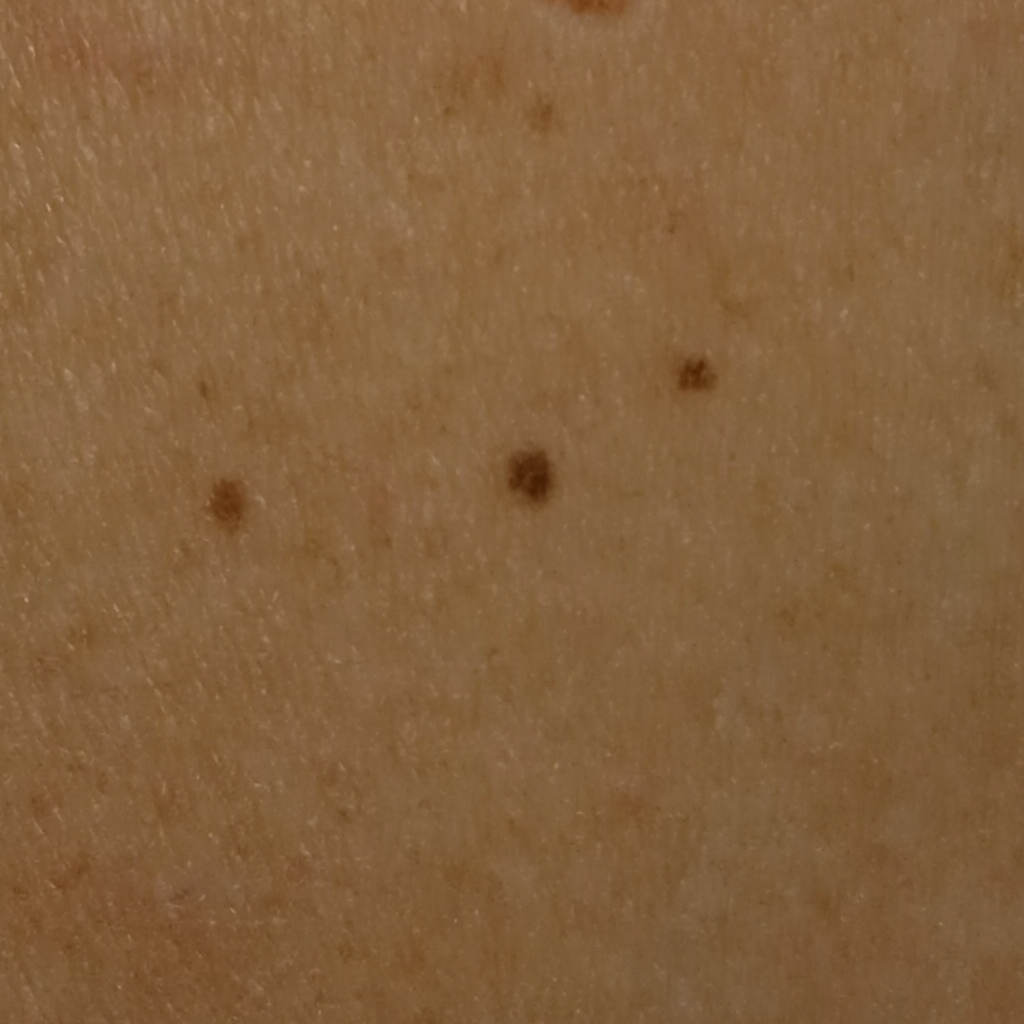A clinical close-up of a skin lesion.
A female subject 50 years of age.
On a questionnaire the patient reported a personal history of skin cancer, no prior organ transplant, and no family history of skin cancer.
Imaged for a research study, with no referral diagnosis recorded.
A moderate number of moles by the patient's own estimate.
The patient says their skin reddens with sun exposure.
The lesion is on an arm.
Dermatologist review favored a melanocytic nevus.